A contact-polarized dermoscopy image of a skin lesion. A female patient roughly 20 years of age. The patient is Fitzpatrick III.
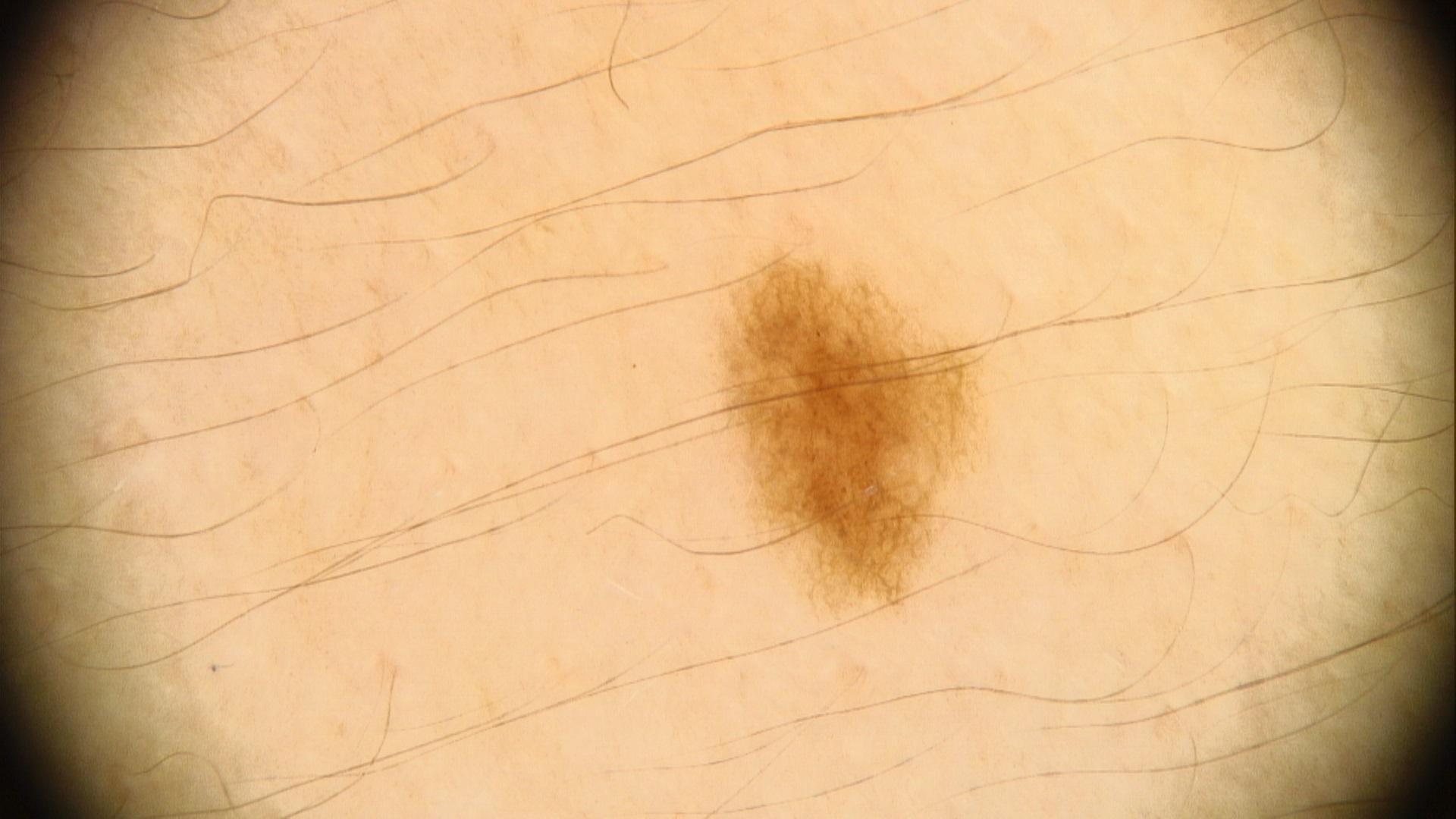diagnosis:
  name: Nevus
  malignancy: benign
  confirmation: expert clinical impression
  lineage: melanocytic